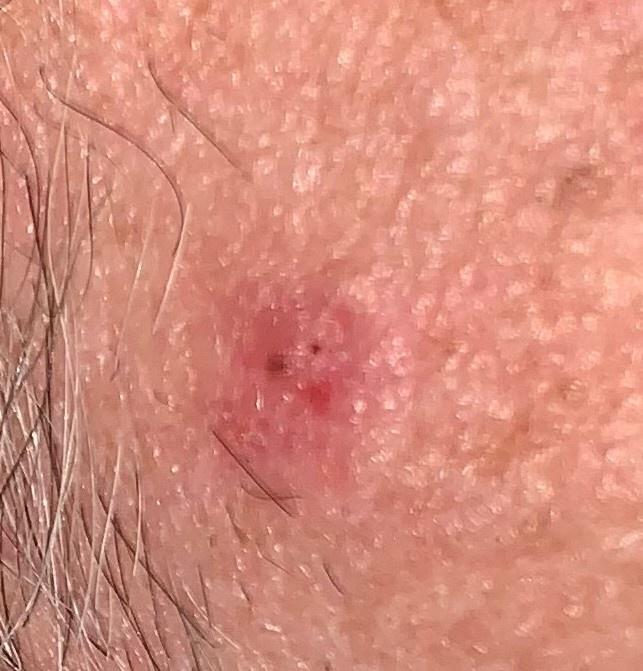A male patient approximately 70 years of age.
Fitzpatrick phototype II.
The lesion involves the head or neck.
Histopathologically confirmed as a basal cell carcinoma.